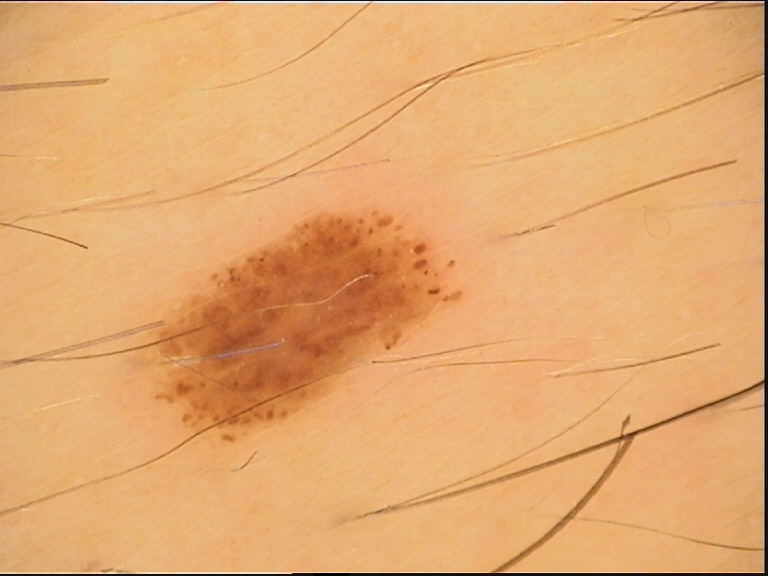Dermoscopy of a skin lesion.
Consistent with a benign lesion — a dysplastic compound nevus.